A close-up photograph. Located on the sole of the foot:
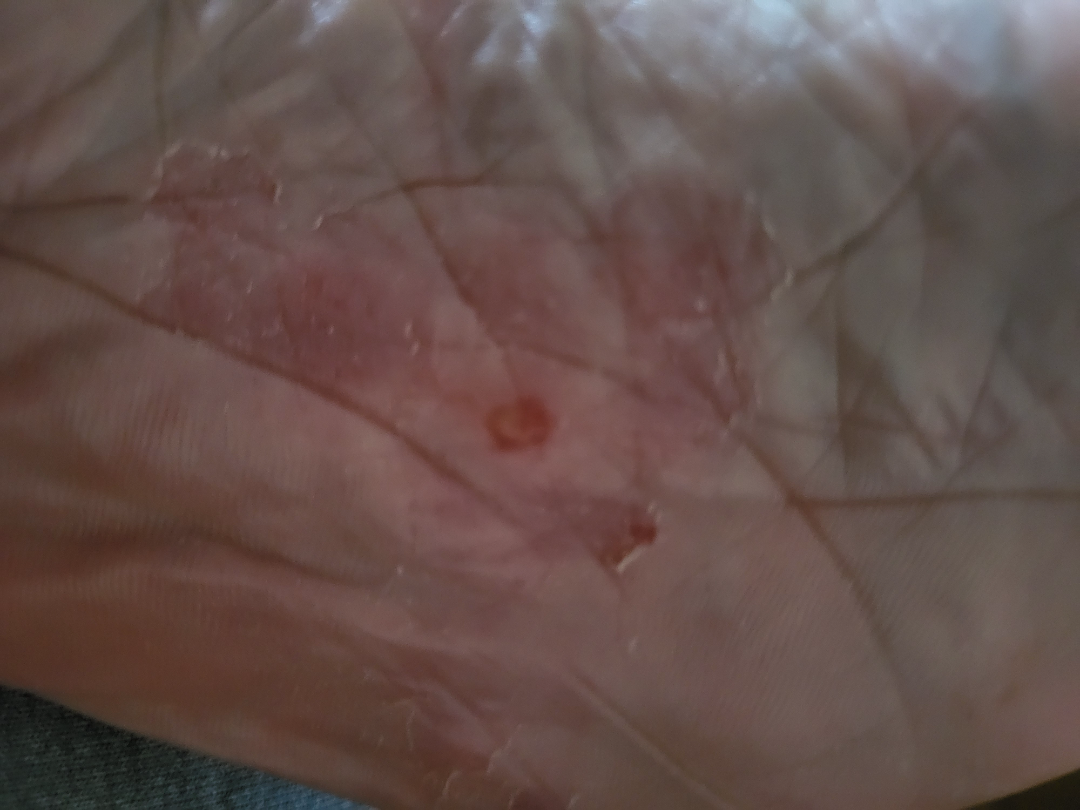Review: Tinea (primary).